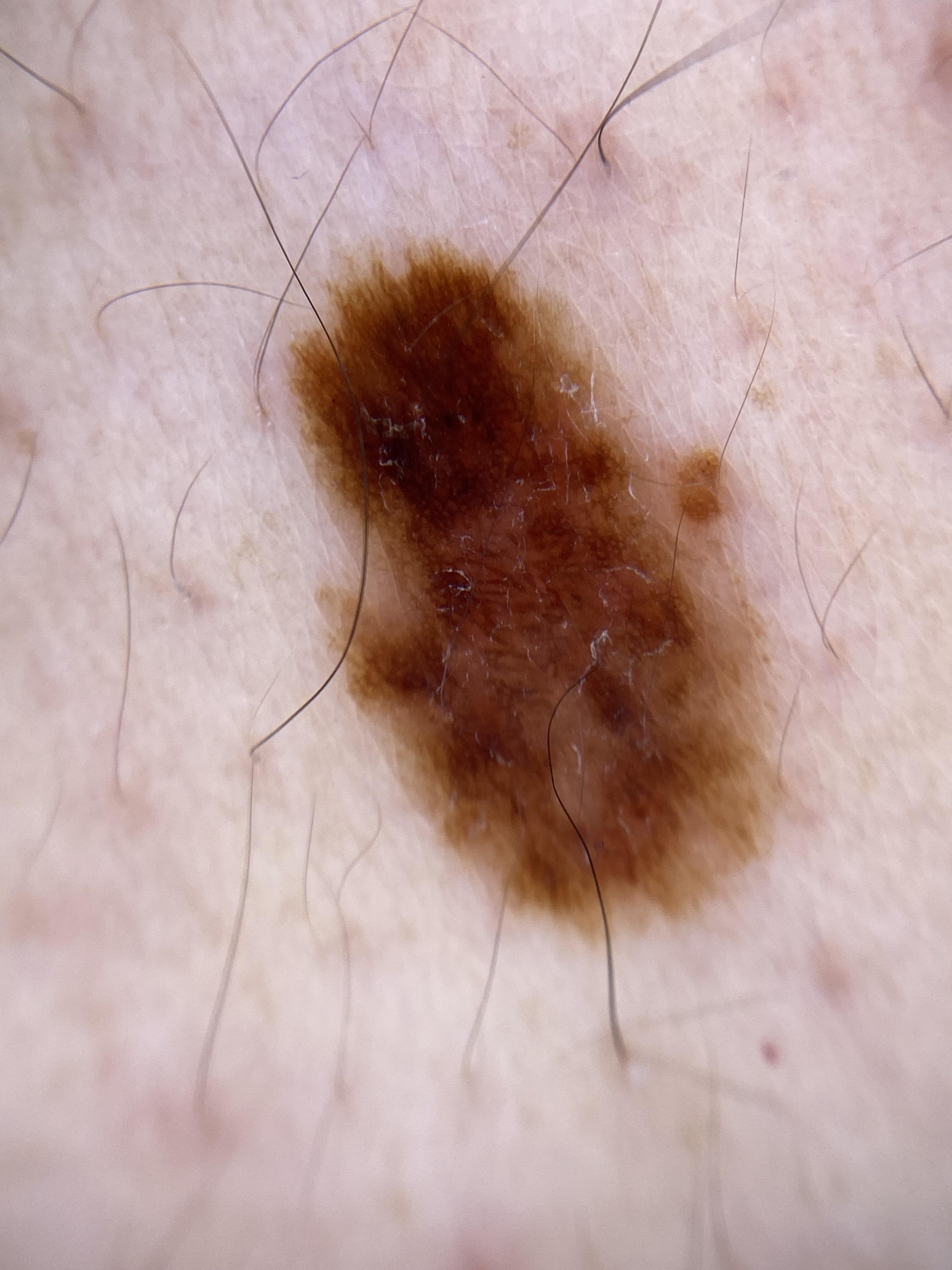image: dermoscopic image
skin_type: II
patient:
  age_approx: 50
  sex: male
diagnosis:
  name: Nevus
  malignancy: benign
  confirmation: histopathology
  lineage: melanocytic